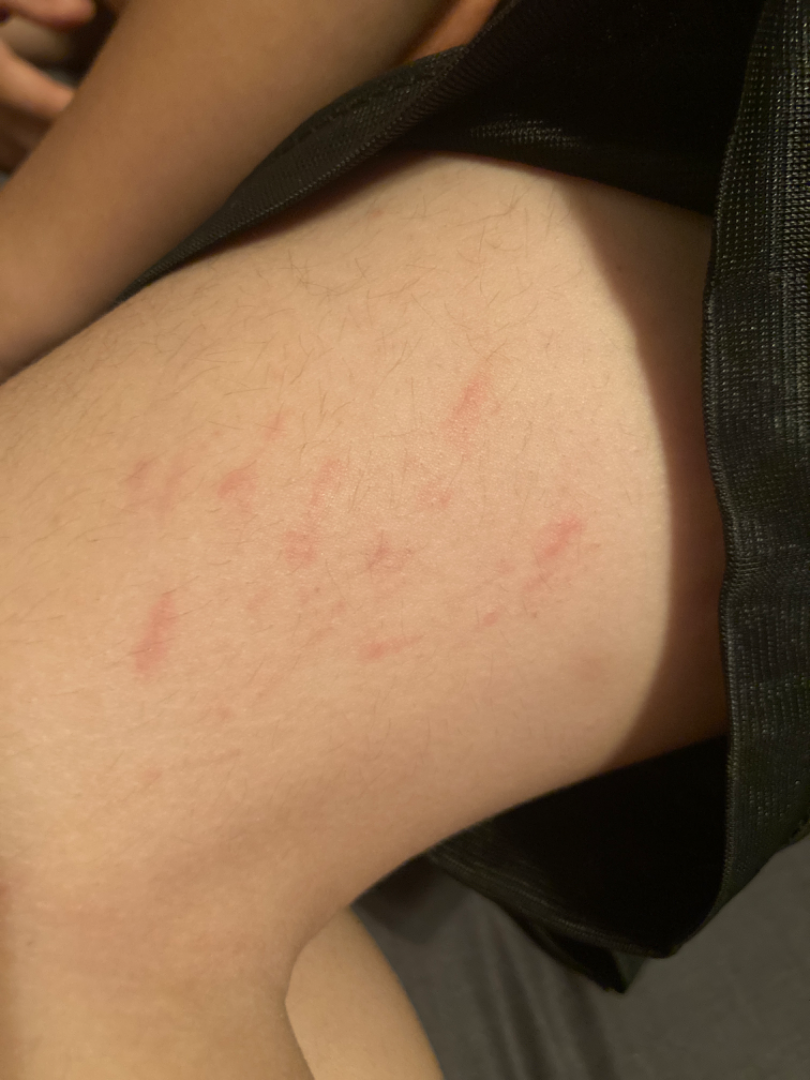The condition could not be reliably identified from the image.
A close-up photograph.